A dermoscopic image of a skin lesion.
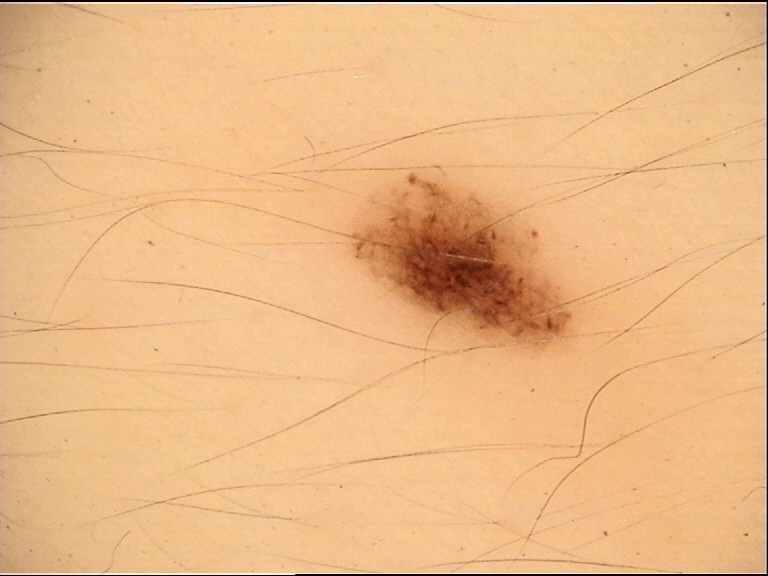{"diagnosis": {"name": "dysplastic junctional nevus", "code": "jd", "malignancy": "benign", "super_class": "melanocytic", "confirmation": "expert consensus"}}